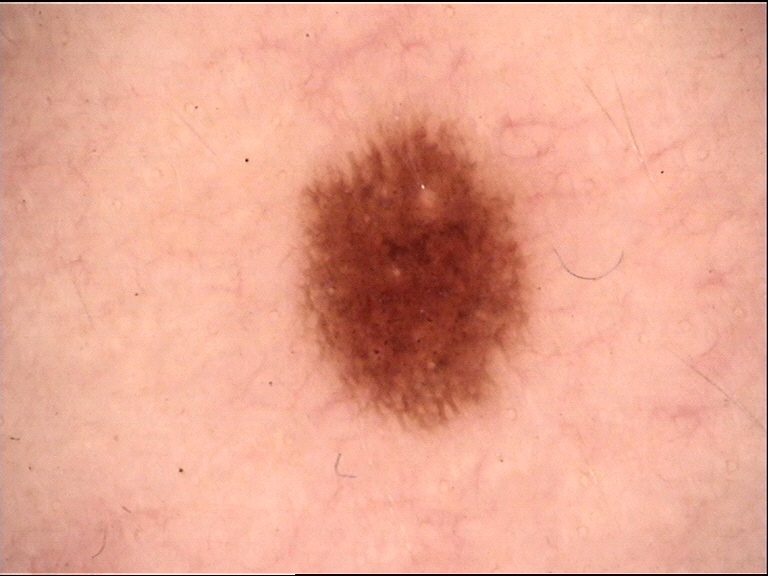class=dysplastic junctional nevus (expert consensus).